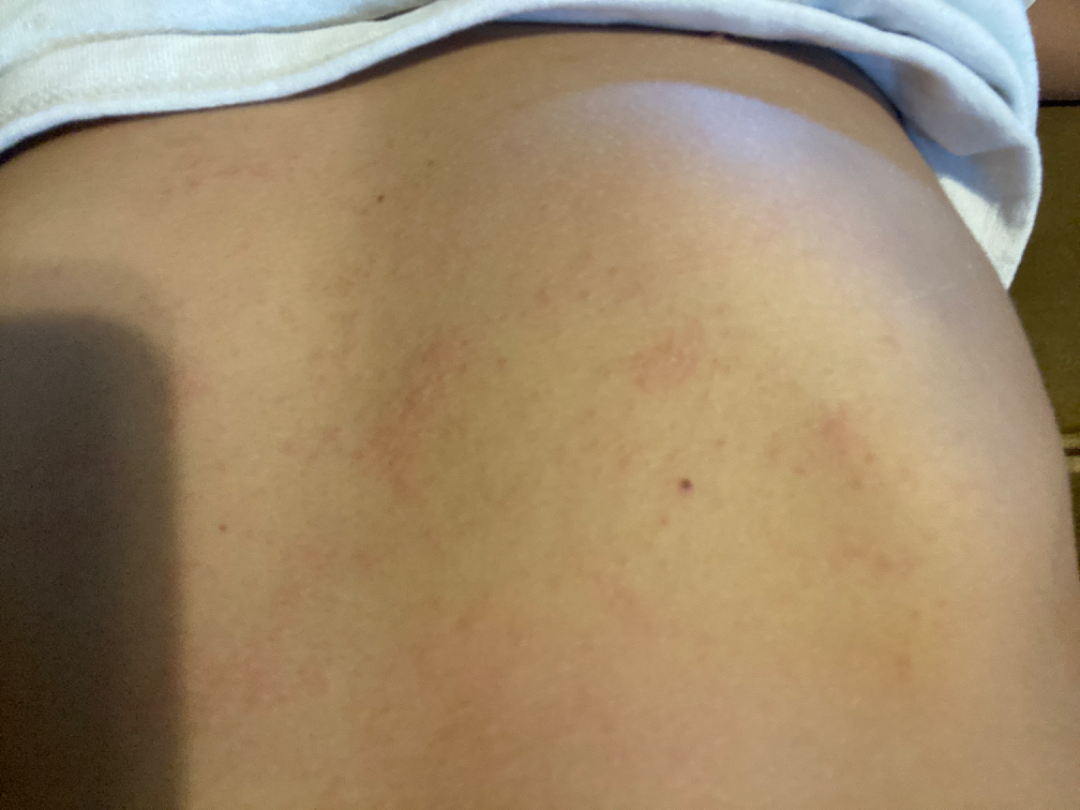{
  "assessment": "not assessable",
  "duration": "one to four weeks",
  "texture": [
    "raised or bumpy",
    "rough or flaky"
  ],
  "skin_tone": {
    "fitzpatrick": "IV"
  },
  "systemic_symptoms": "none reported",
  "shot_type": "at an angle",
  "body_site": [
    "back of the torso",
    "arm",
    "front of the torso"
  ],
  "patient_category": "a rash",
  "symptoms": [
    "itching",
    "bothersome appearance"
  ]
}